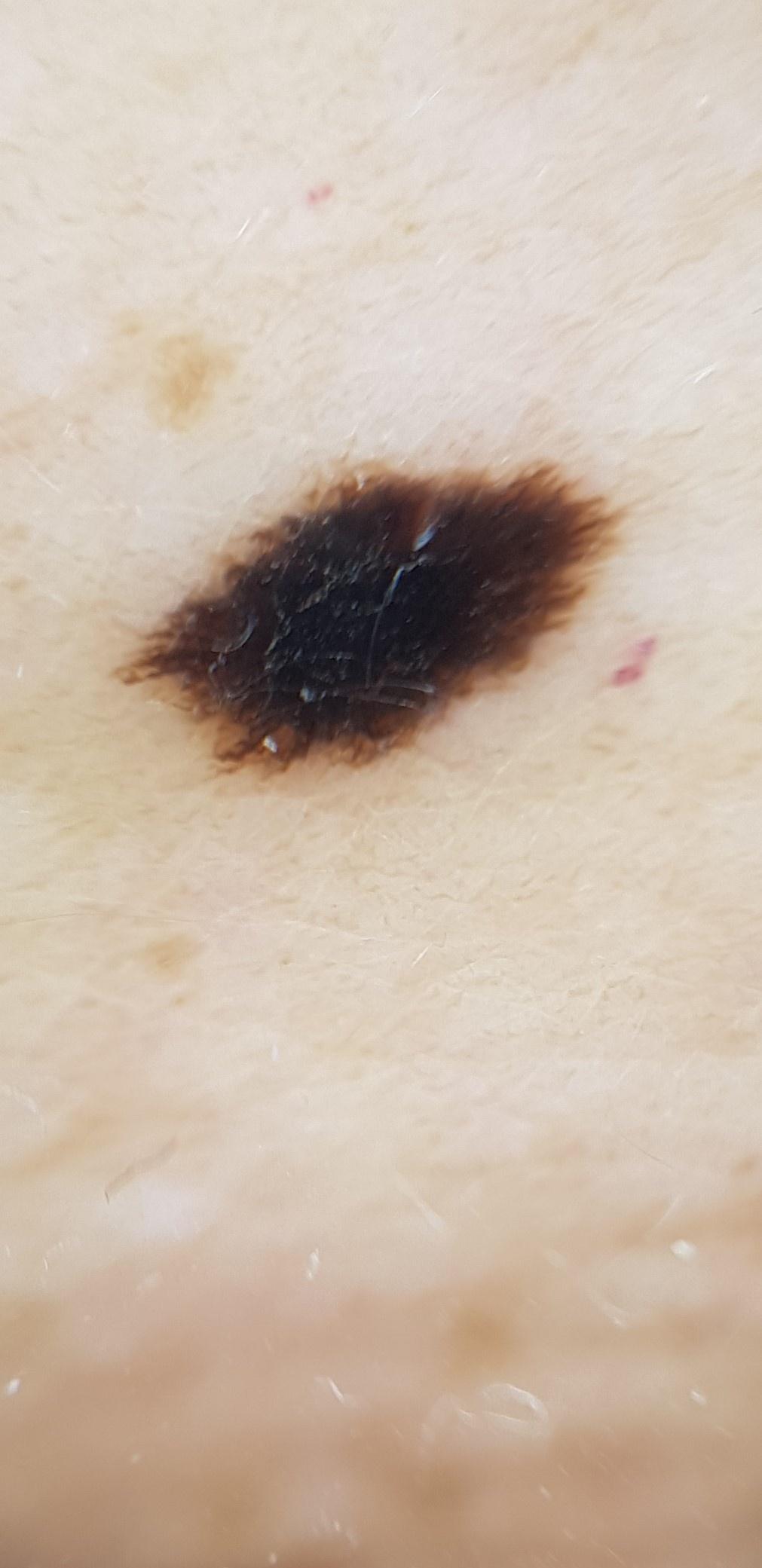Case:
• image · dermatoscopic image
• subject · female, aged 58 to 62
• location · the trunk
• pathology · Nevus (biopsy-proven)